A clinical photograph showing a skin lesion. A male patient in their late 60s.
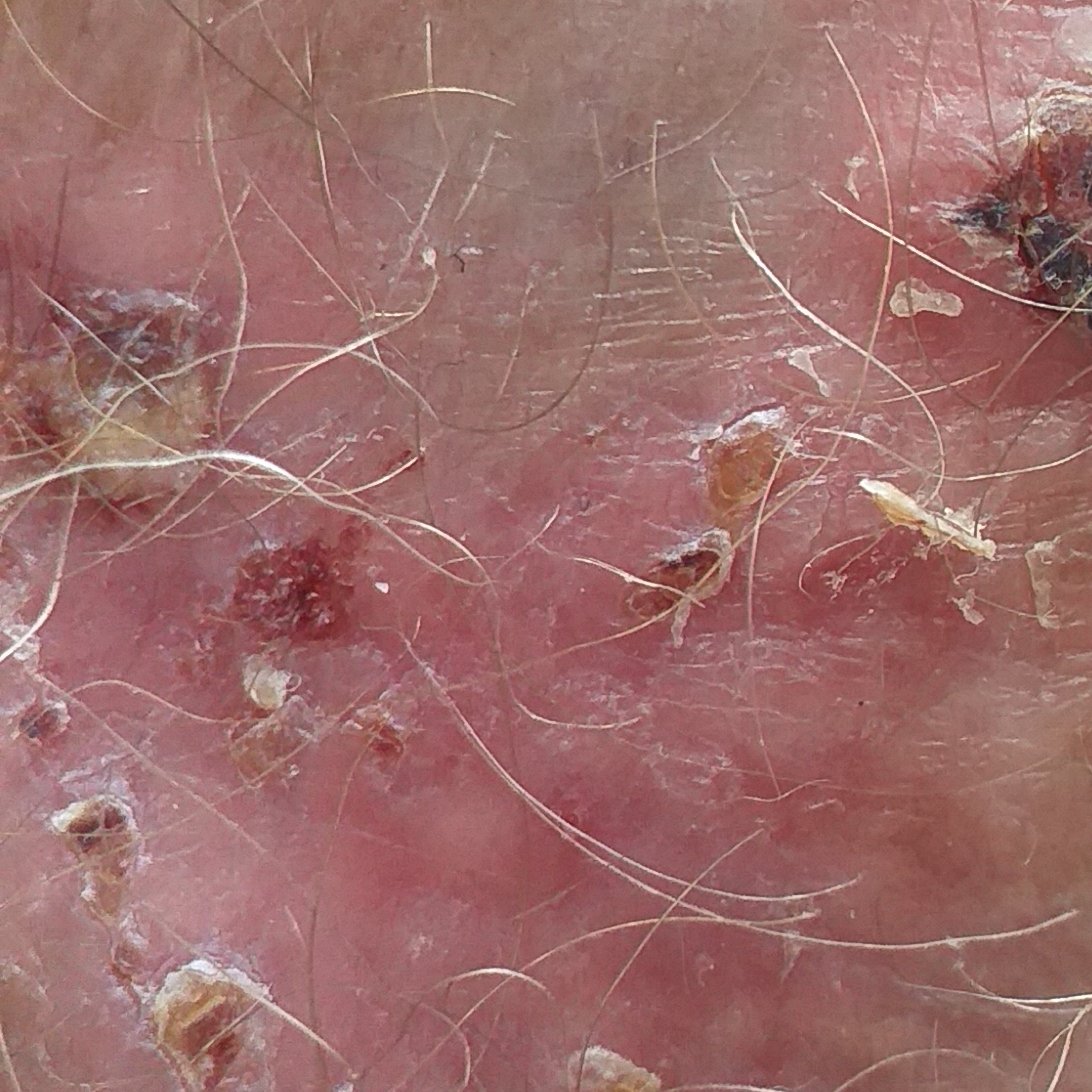• location · a forearm
• diagnostic label · basal cell carcinoma (biopsy-proven)